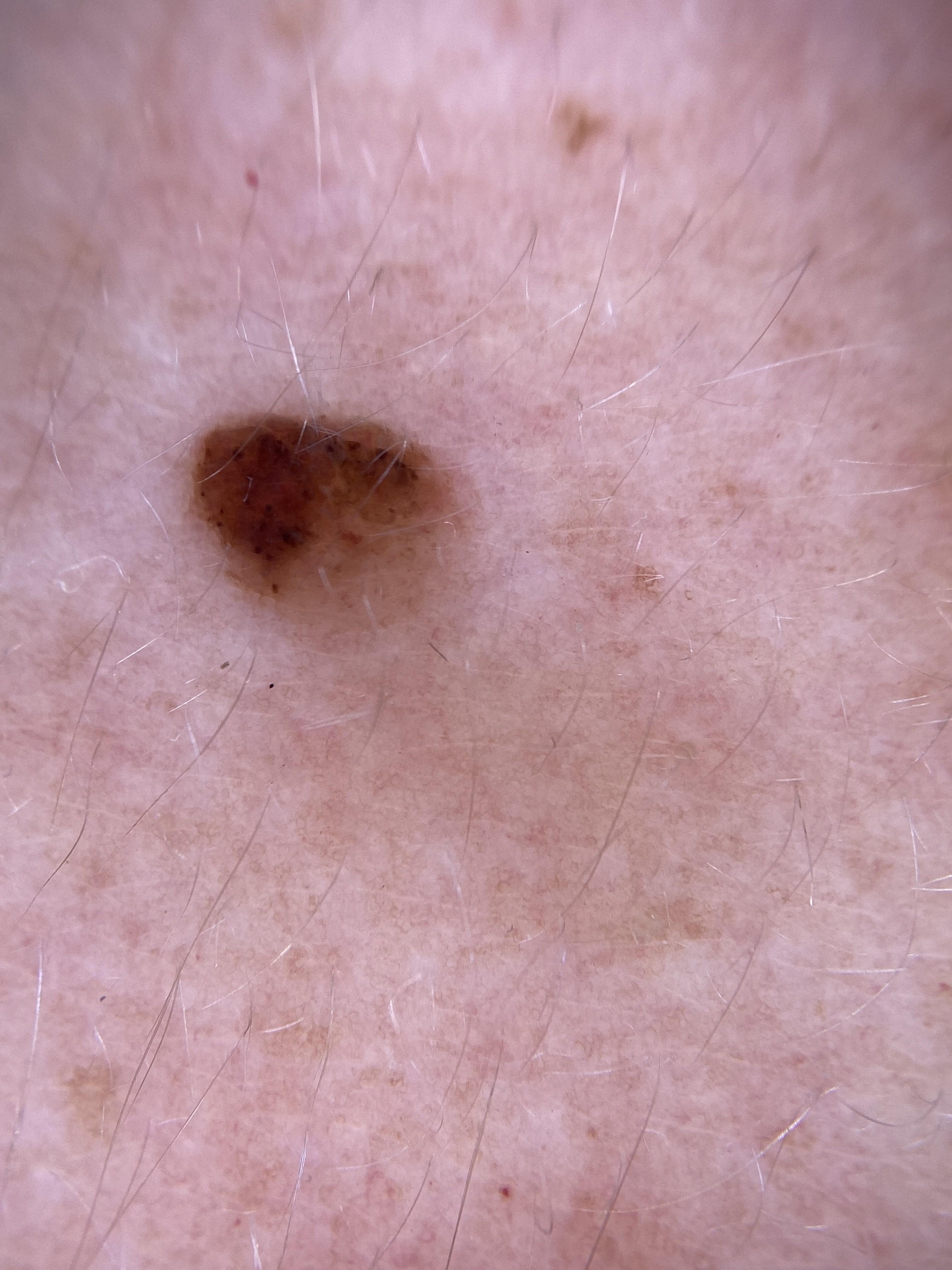<record>
<patient>
<age_approx>35</age_approx>
<sex>female</sex>
</patient>
<lesion_location>
<region>the trunk</region>
<detail>the posterior trunk</detail>
</lesion_location>
<diagnosis>
<name>Nevus</name>
<malignancy>benign</malignancy>
<confirmation>expert clinical impression</confirmation>
<lineage>melanocytic</lineage>
</diagnosis>
</record>